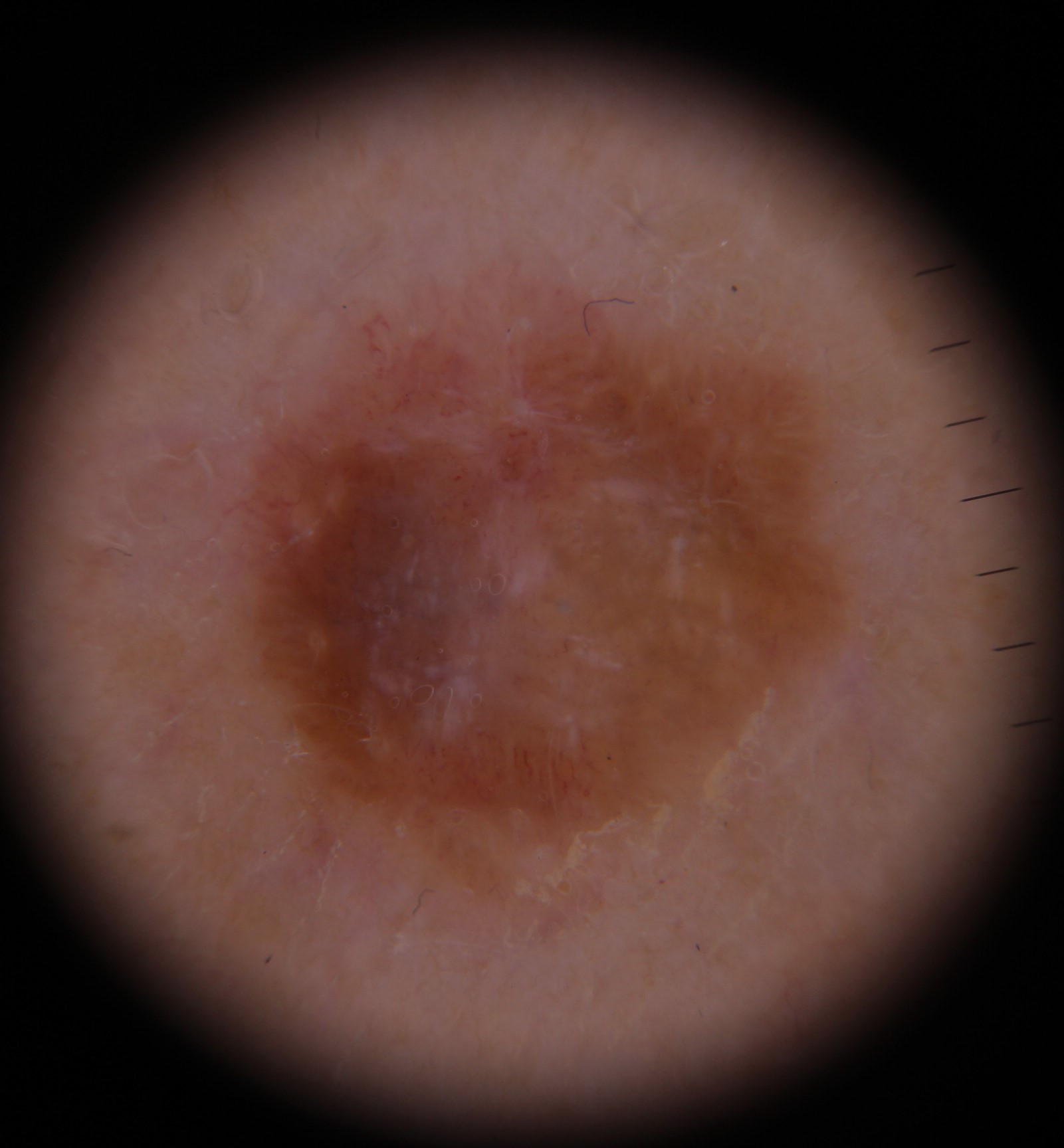Histopathology confirmed a melanoma.